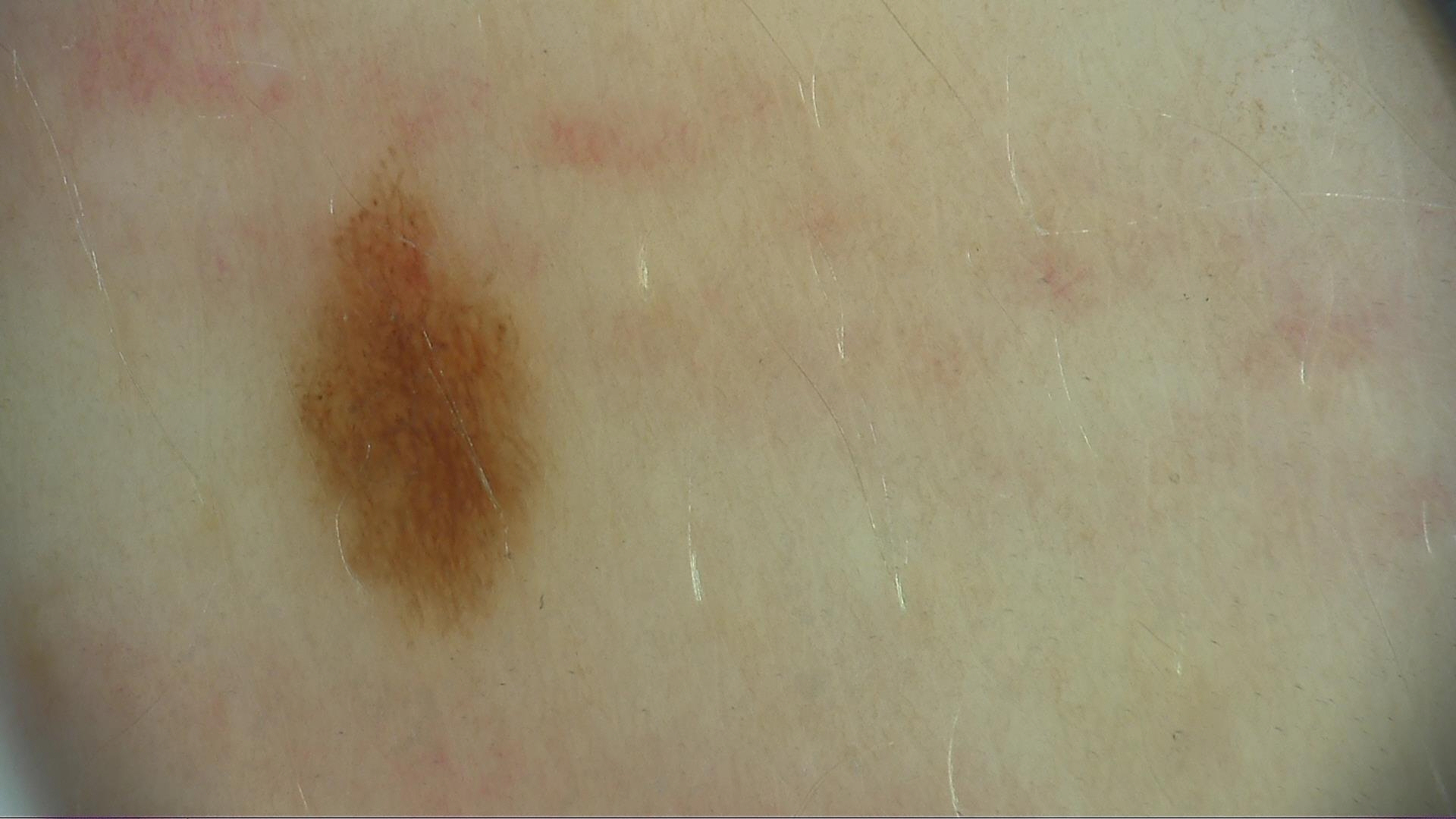label = dysplastic junctional nevus (expert consensus)